The contributor is 30–39, female · this image was taken at a distance · the affected area is the head or neck — 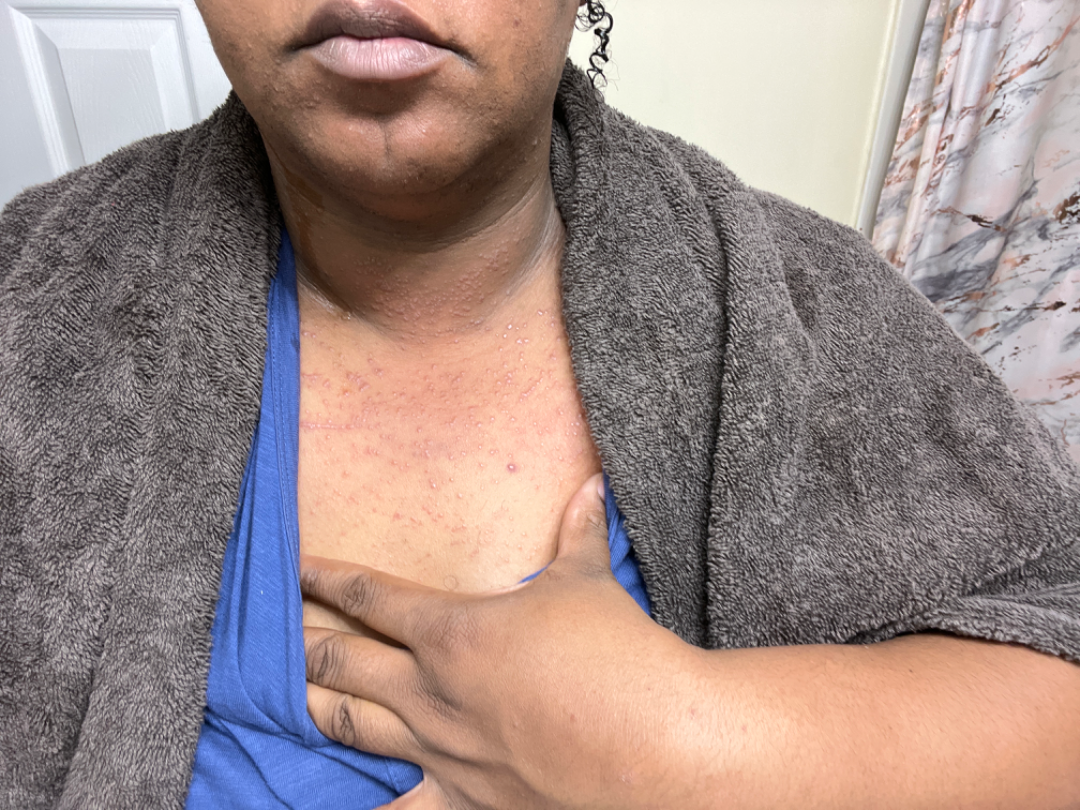assessment — most consistent with Adnexal neoplasm; possibly Folliculitis; also consider Miliaria; a more distant consideration is Cyst; less probable is Lichen planus/lichenoid eruption